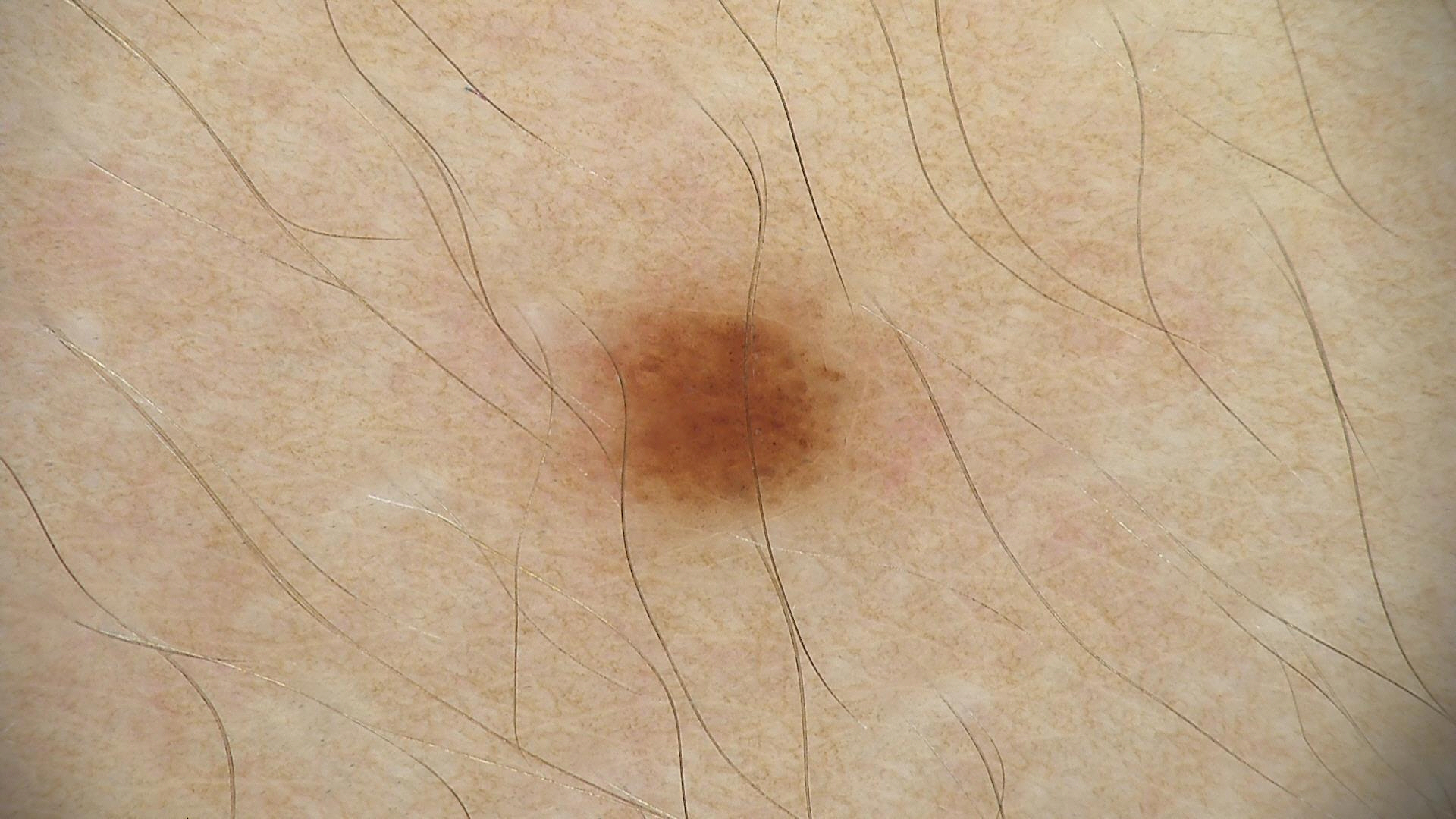Findings: A dermoscopic photograph of a skin lesion. Conclusion: Consistent with a dysplastic junctional nevus.